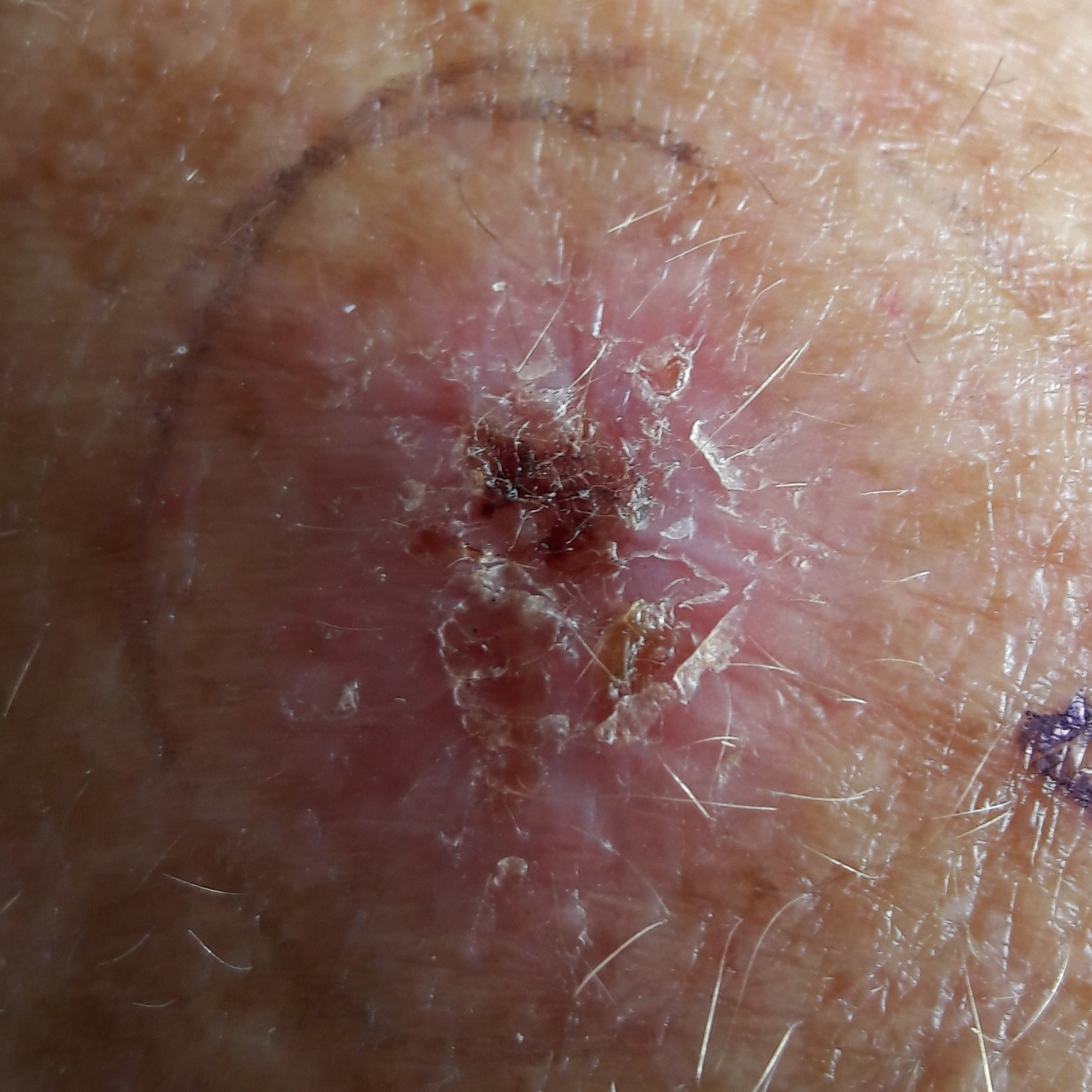{"risk_factors": {"positive": ["prior skin cancer (patient or family)"]}, "skin_type": "II", "patient": {"age": 53, "gender": "female"}, "lesion_location": "a forearm", "lesion_size": {"diameter_1_mm": 20.0, "diameter_2_mm": 15.0}, "symptoms": {"present": ["growth", "pain", "bleeding", "itching", "elevation"]}, "diagnosis": {"name": "actinic keratosis", "code": "ACK", "malignancy": "indeterminate", "confirmation": "histopathology"}}